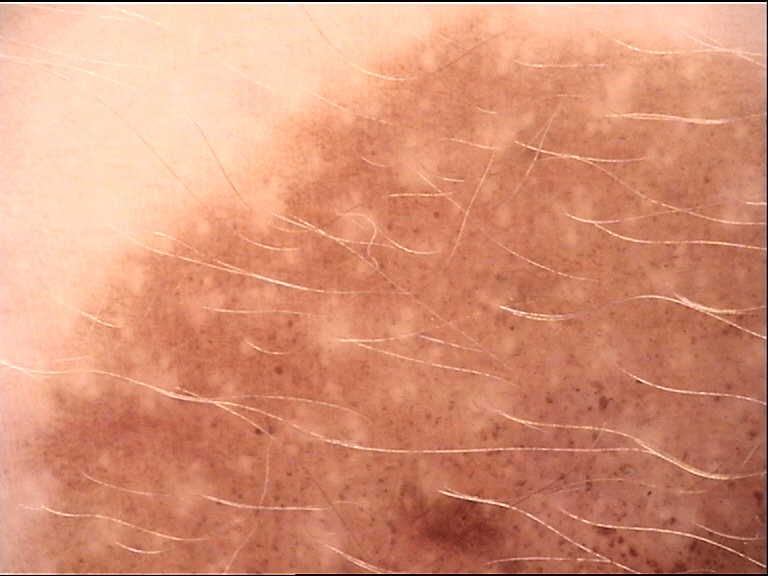Conclusion:
Consistent with a congenital junctional nevus.